Dermoscopy of a skin lesion.
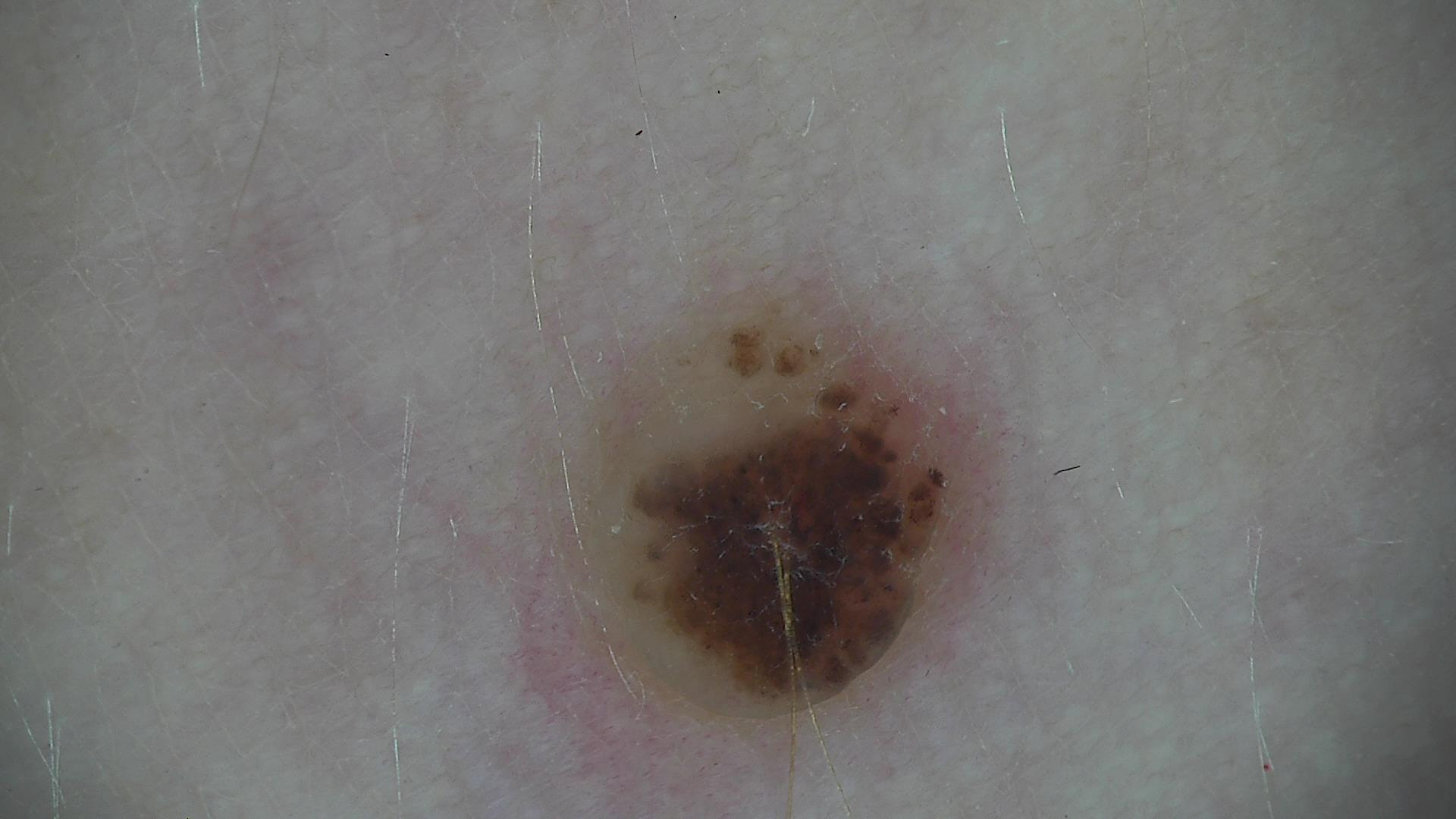category=banal
diagnostic label=compound nevus (expert consensus)